A dermoscopic close-up of a skin lesion.
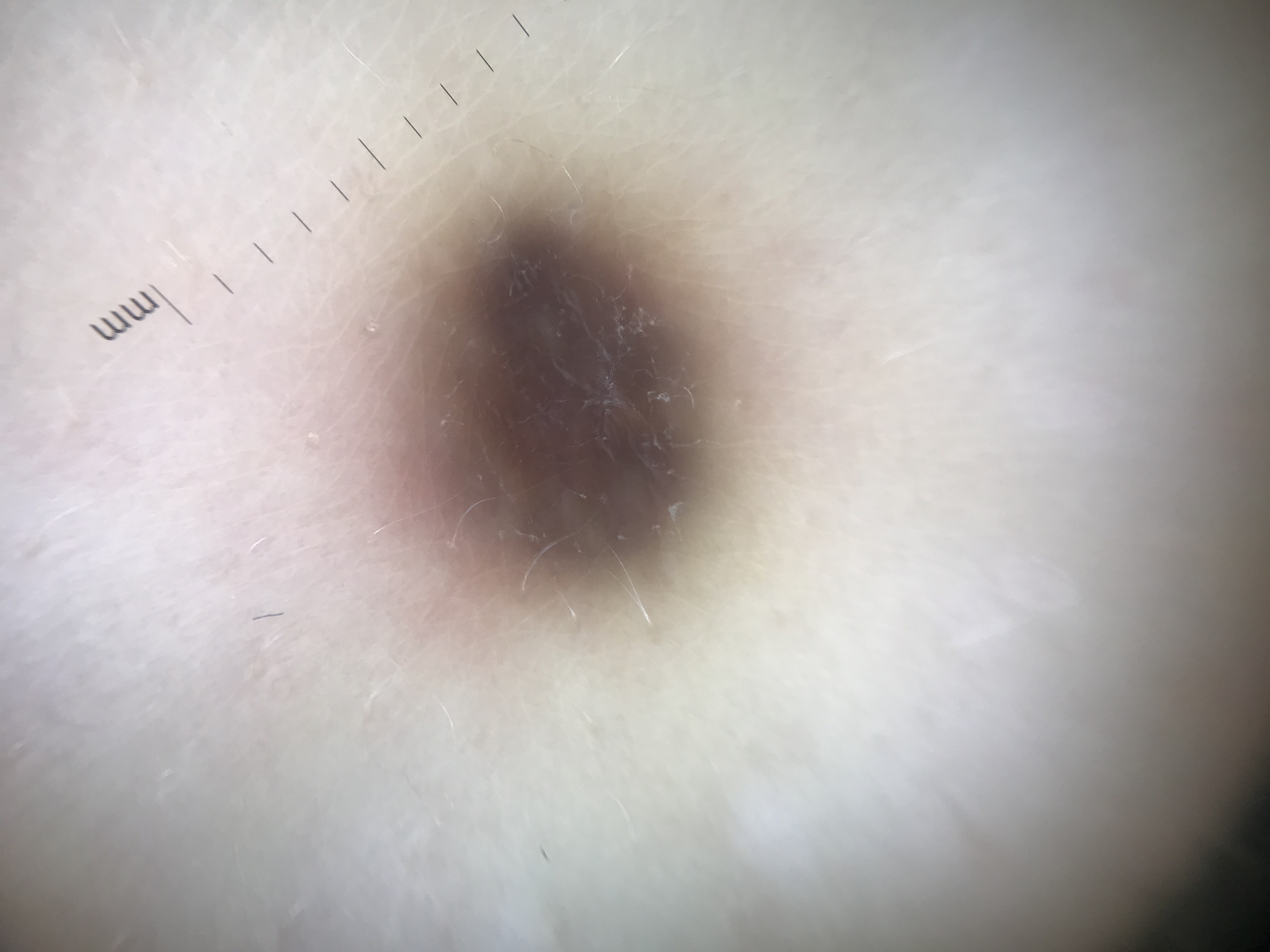Impression:
Consistent with a dermal lesion — a blue nevus.